An image taken at a distance · the lesion involves the arm, head or neck and front of the torso · the contributor is 18–29, male — 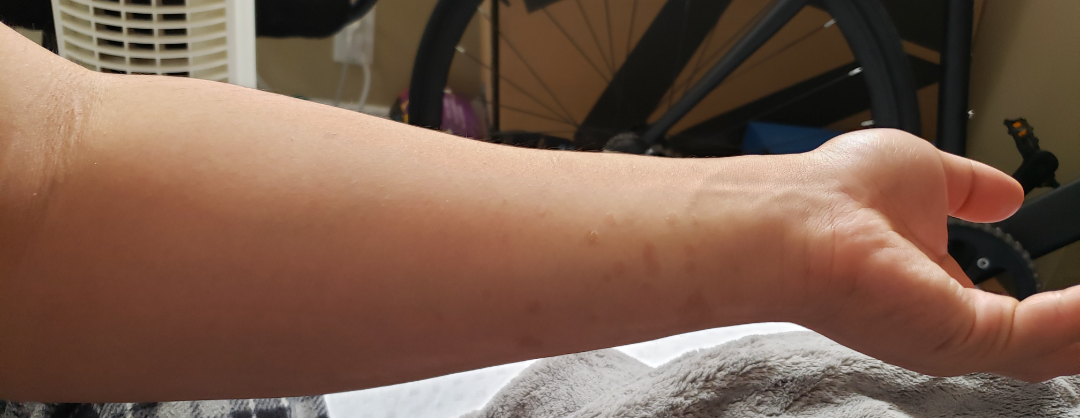| field | value |
|---|---|
| patient describes the issue as | a rash |
| present for | more than one year |
| described texture | flat and rough or flaky |
| impression | the differential is split between Psoriasis and Syphilis; an alternative is Tinea Versicolor; less likely is Pityriasis rosea |